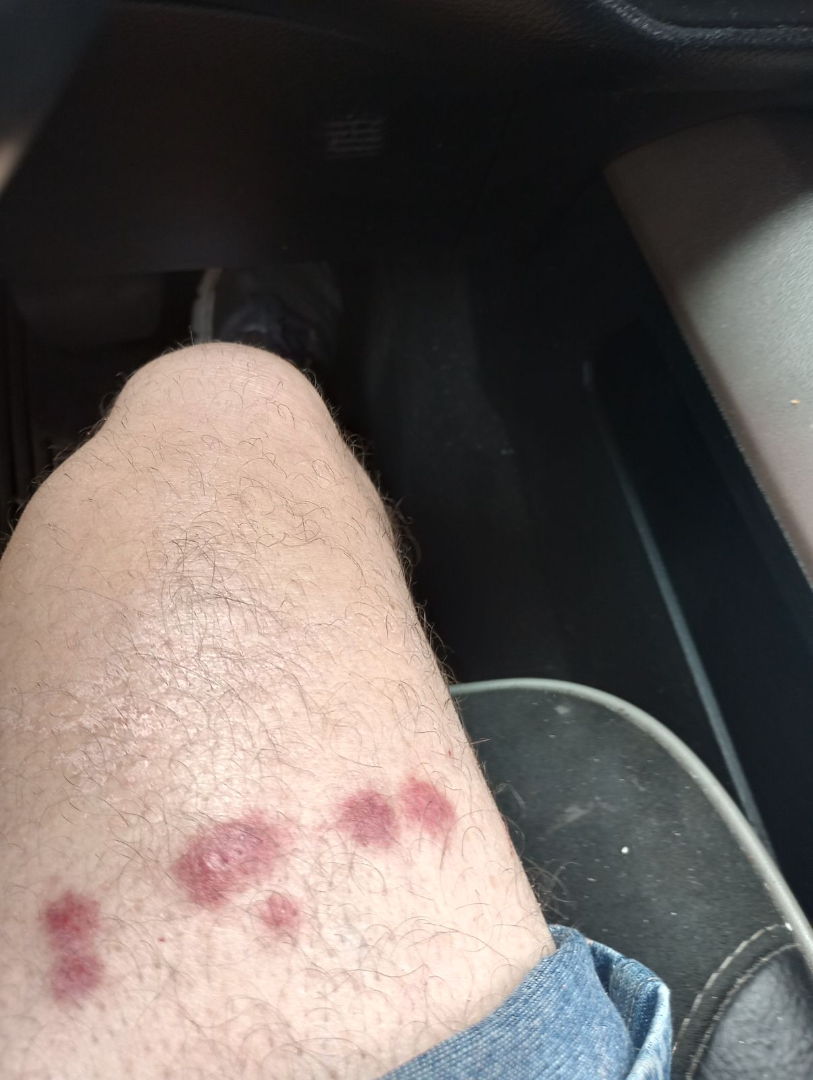{"assessment": "could not be assessed"}